A female subject aged 60 · a dermoscopy image of a skin lesion · acquired for a research image collection, with no referral diagnosis: 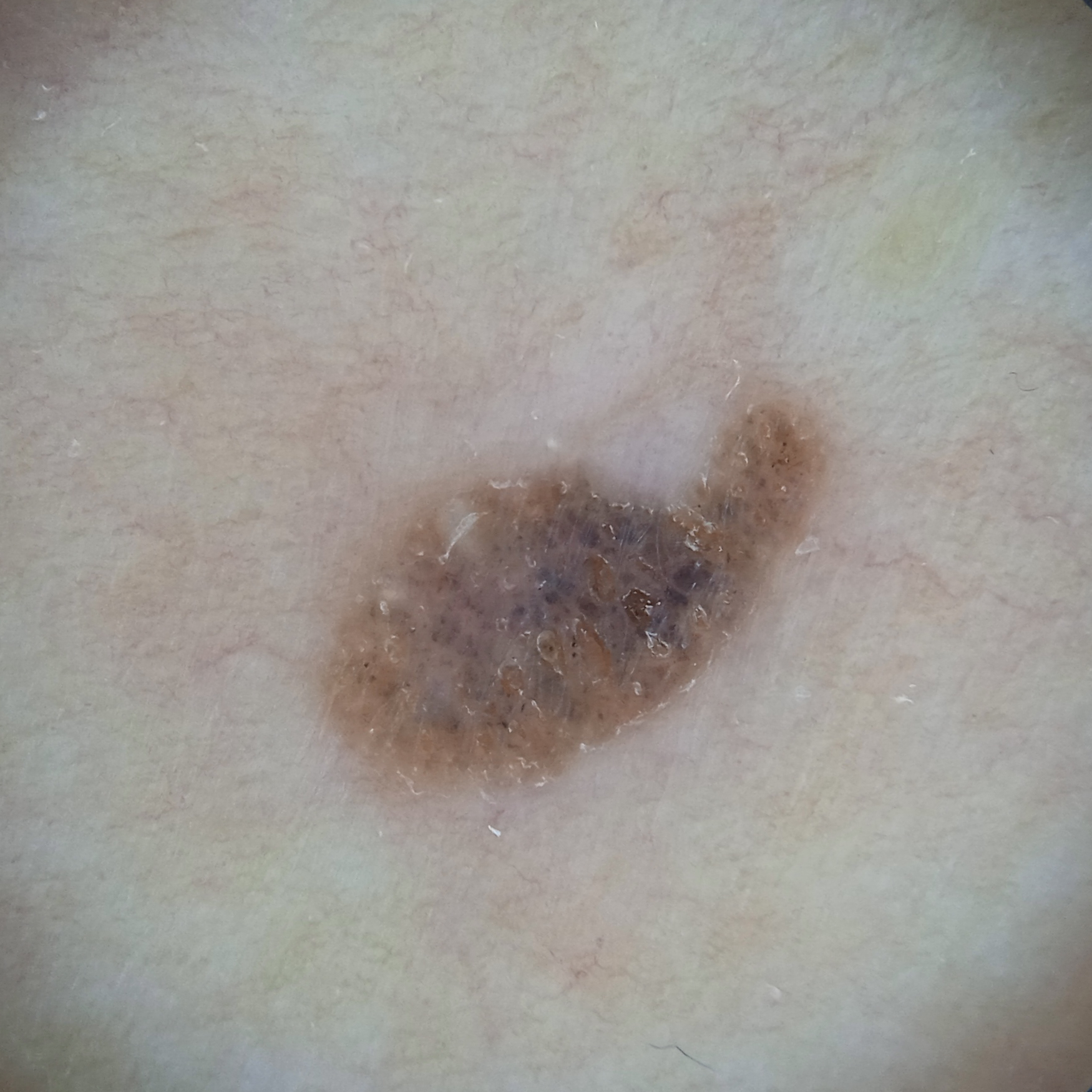Findings:
* location: the torso
* size: 6.2 mm
* assessment: seborrheic keratosis (dermatologist consensus)